The arm is involved · the contributor is a male aged 40–49 · a close-up photograph.
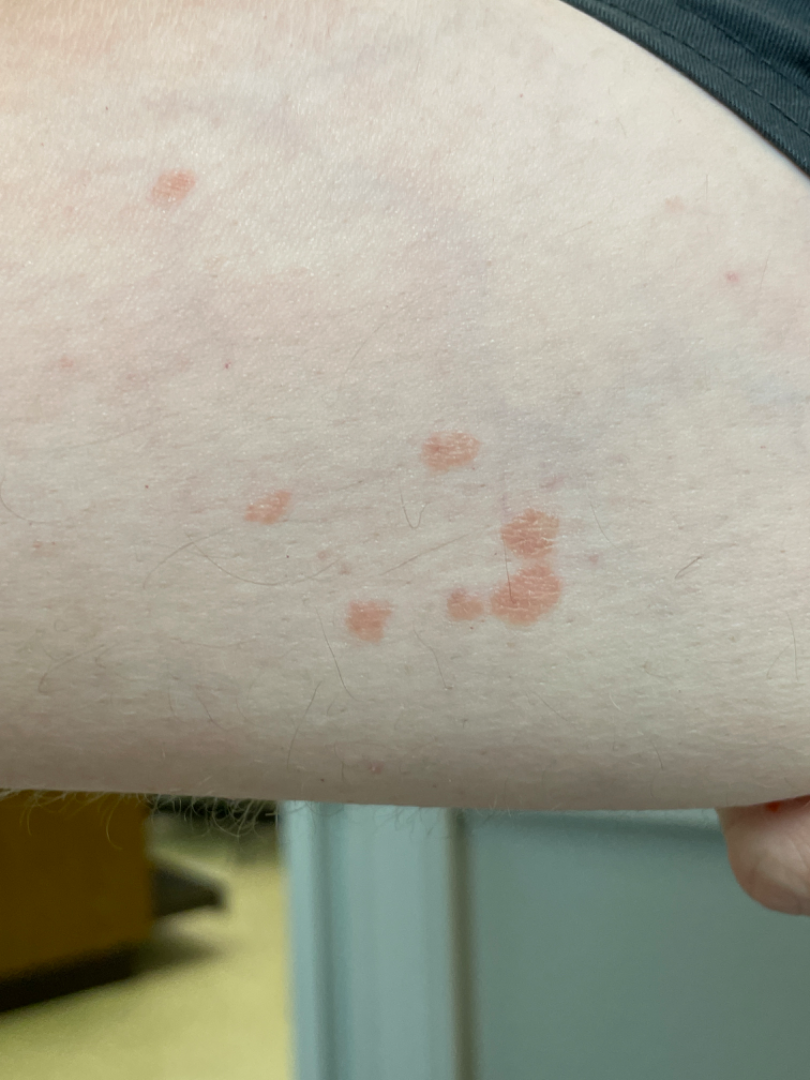dermatologist impression: Tinea (possible); Psoriasis (possible); Tinea Versicolor (possible).